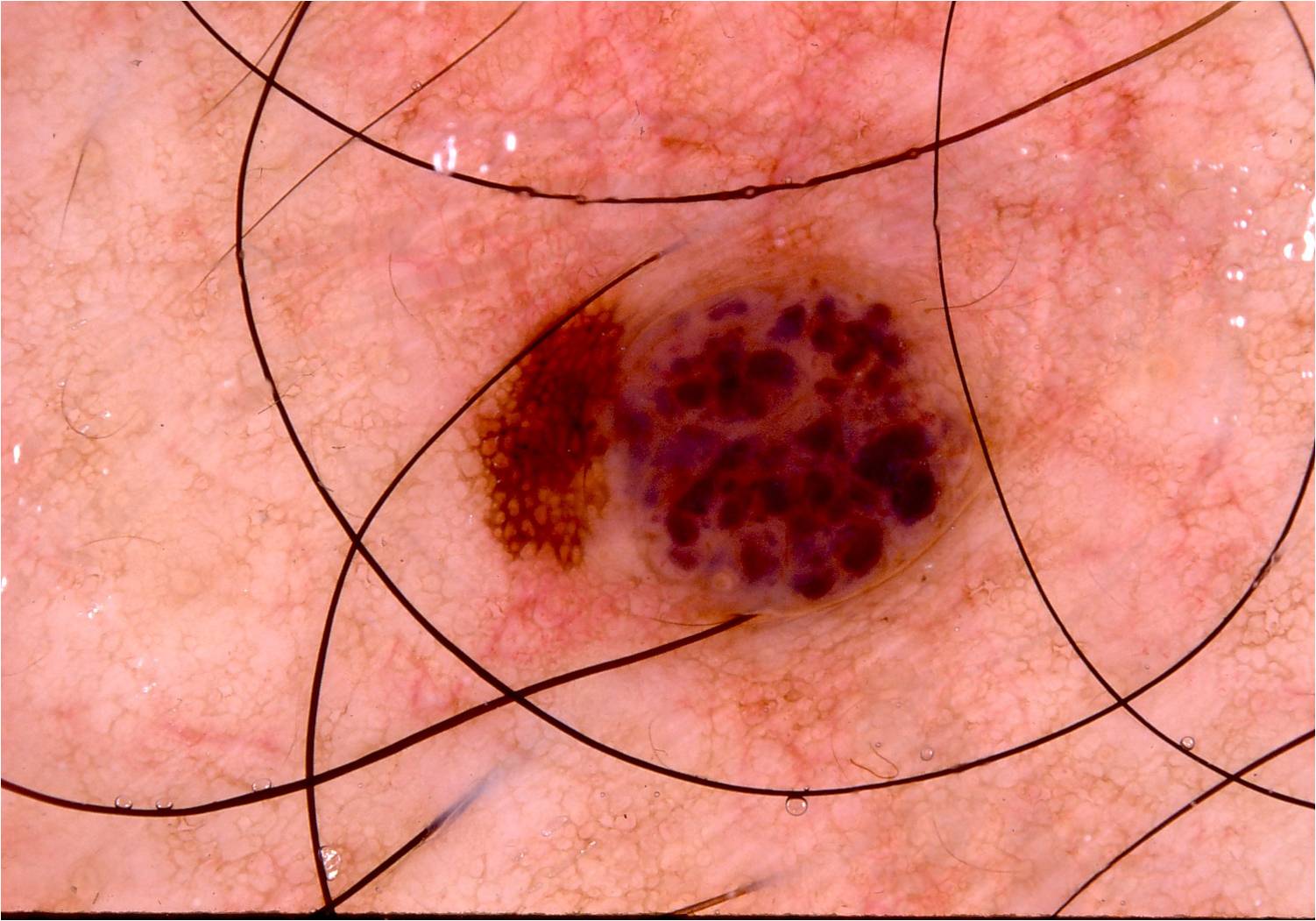{"image": {"modality": "dermoscopy"}, "lesion_extent": {"approx_field_fraction_pct": 13}, "dermoscopic_features": {"present": ["pigment network"], "absent": ["negative network", "globules", "milia-like cysts", "streaks"]}, "lesion_location": {"bbox_xyxy": [450, 251, 997, 623]}, "diagnosis": {"name": "melanocytic nevus", "malignancy": "benign", "lineage": "melanocytic", "provenance": "clinical"}}